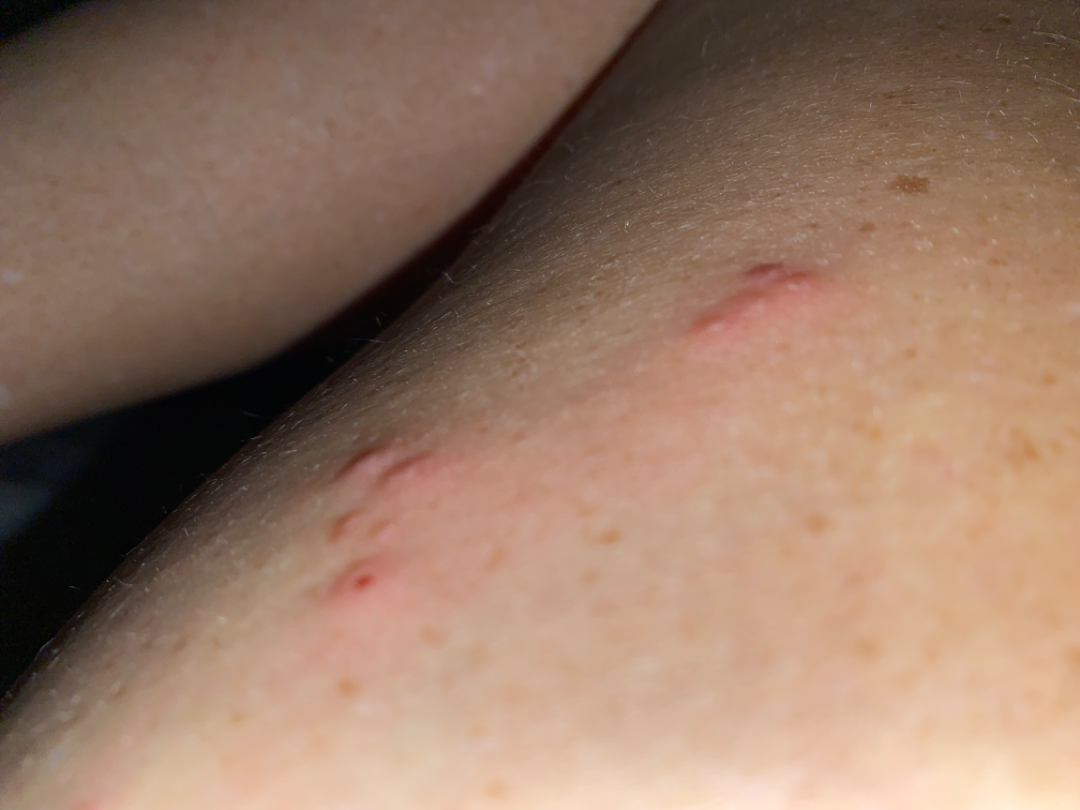Case summary:
* assessment · not assessable
* body site · back of the torso and leg
* photo taken · at an angle